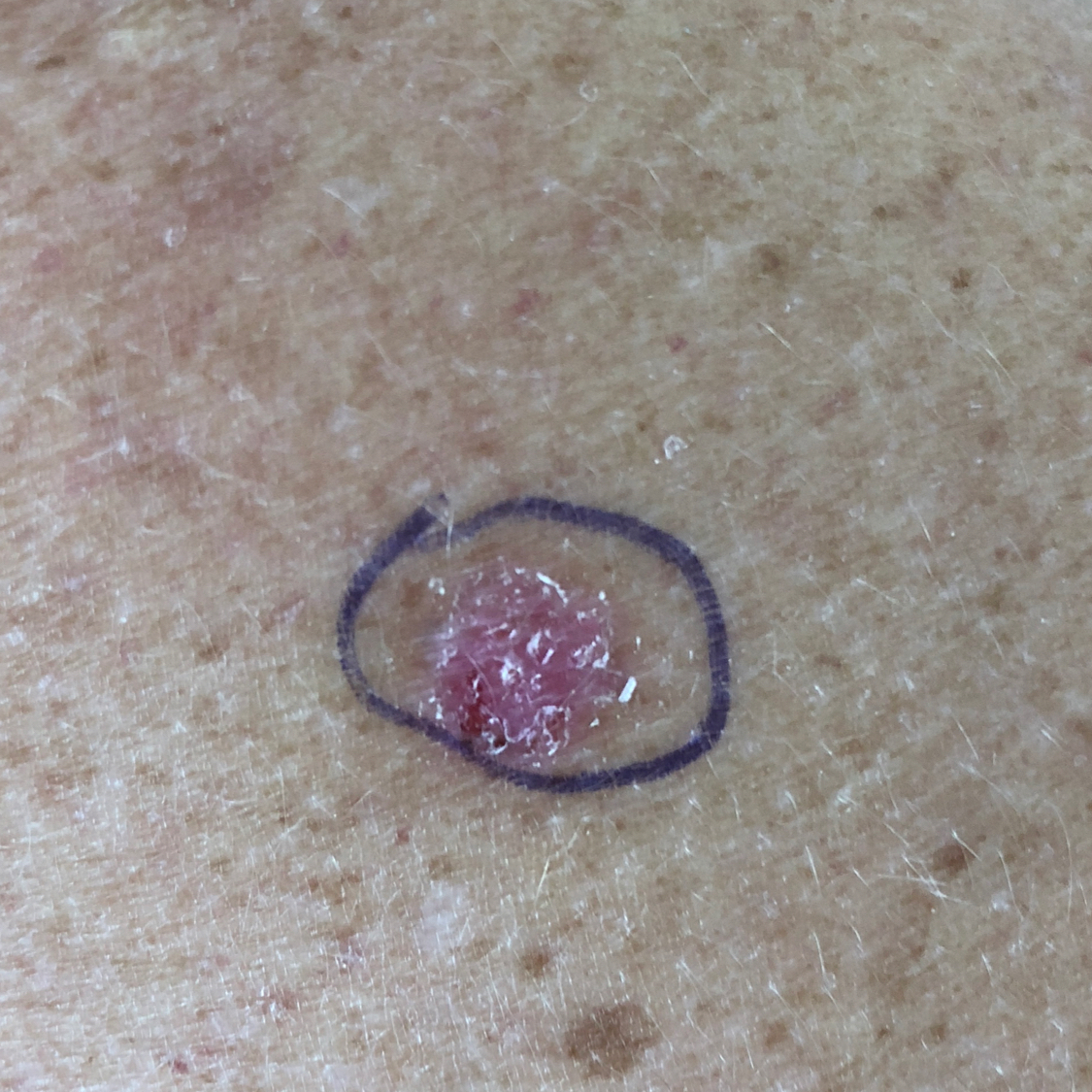Case summary:
A subject in their 30s. A clinical close-up photograph of a skin lesion. The lesion is on an arm. Per patient report, the lesion itches.
Conclusion:
Expert review favored an actinic keratosis.